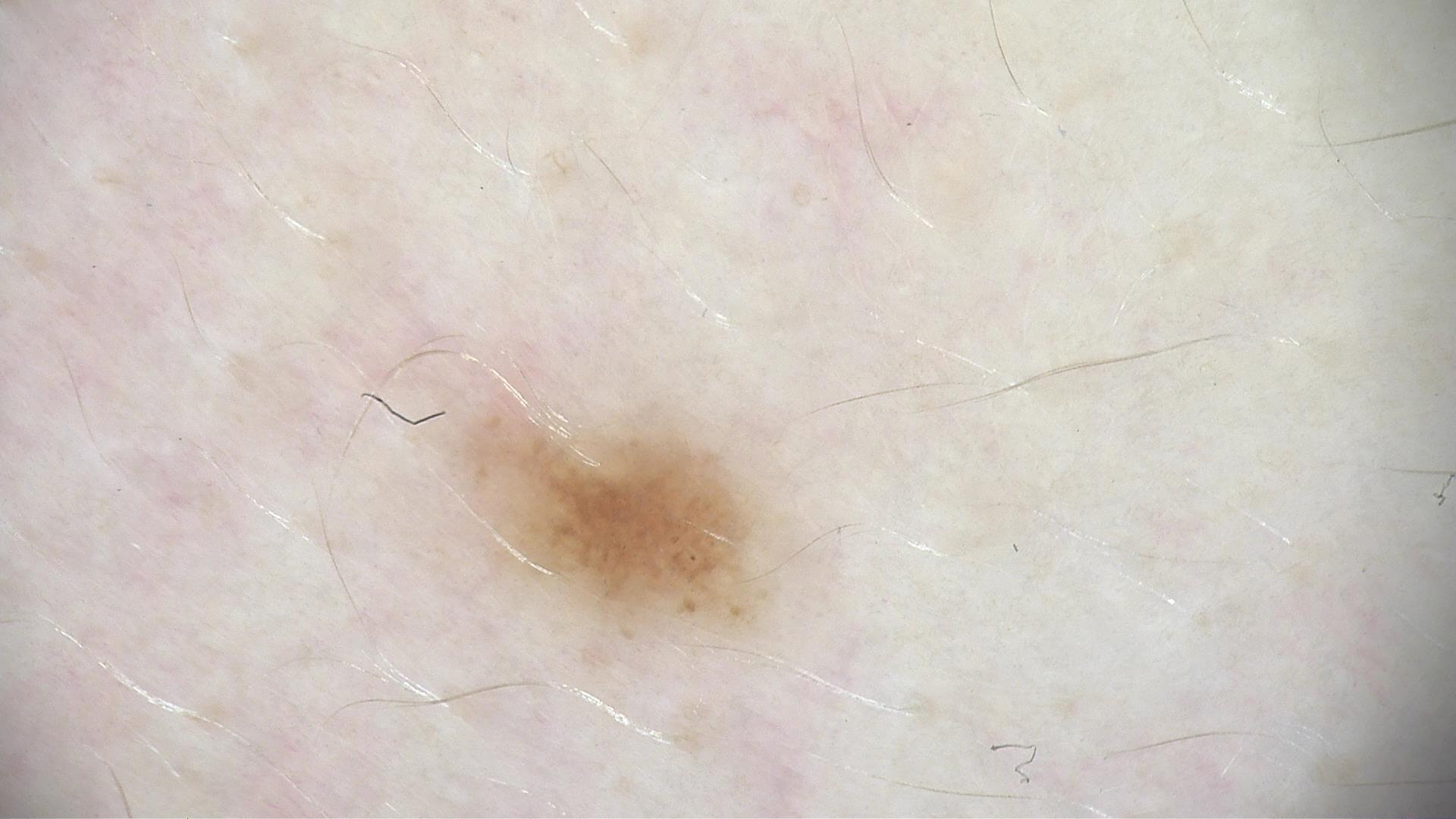A dermoscopy image of a single skin lesion.
Consistent with a dysplastic junctional nevus.